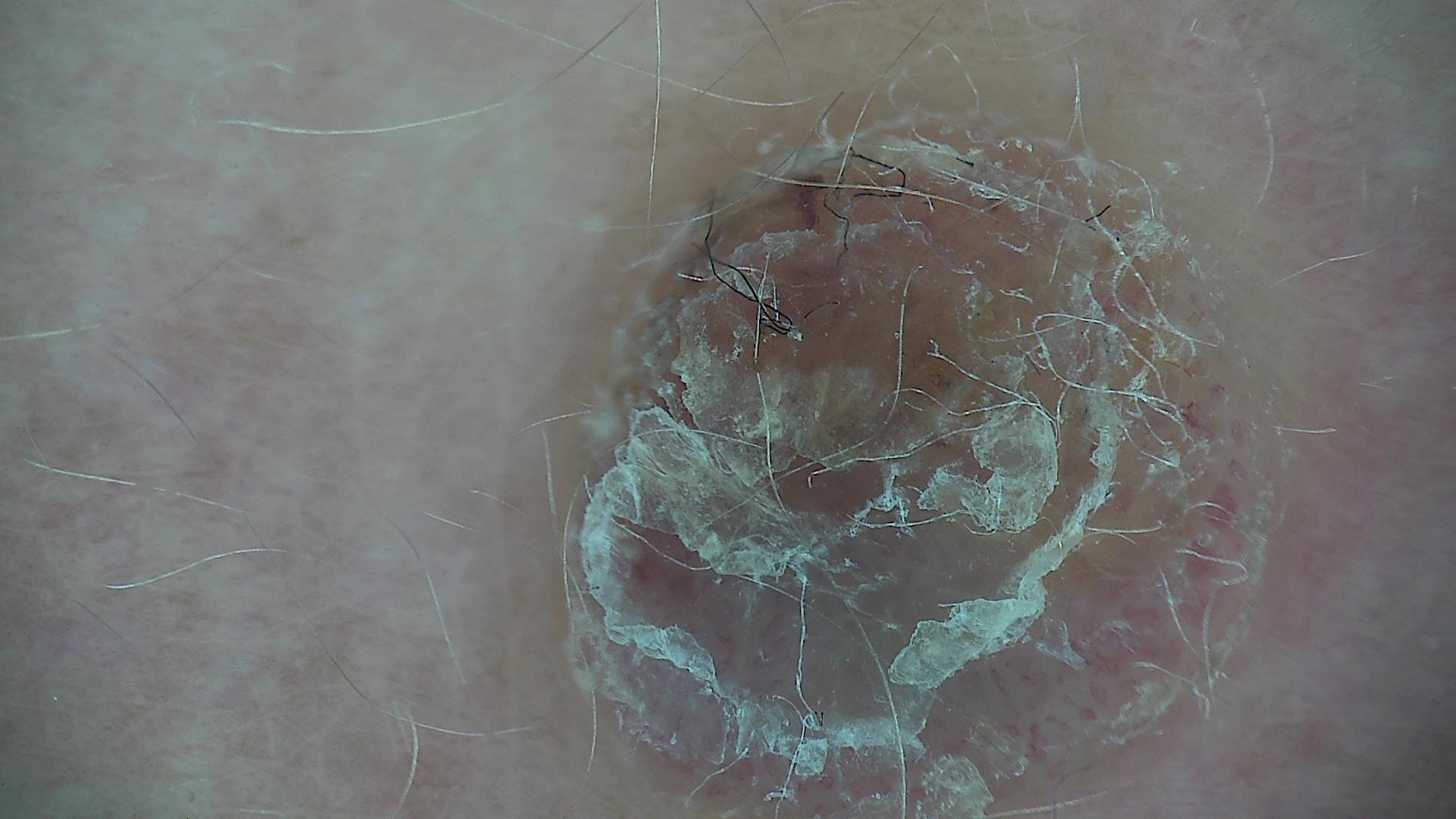diagnostic label = dermatofibroma (expert consensus)